The patient is a female aged 18–29 · this is a close-up image · the affected area is the leg · the contributor notes the condition has been present for one to four weeks · self-categorized by the patient as a rash · the lesion is described as raised or bumpy and rough or flaky · no associated lesion symptoms were reported:
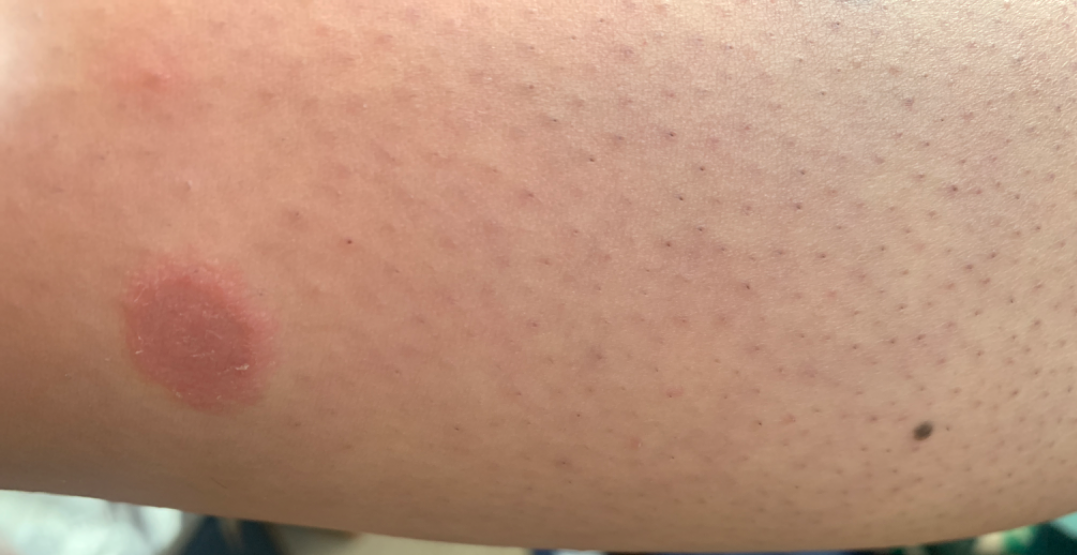Q: What is the differential diagnosis?
A: the leading consideration is Eczema; also raised was Psoriasis; also on the differential is Tinea; less likely is Pityriasis rosea